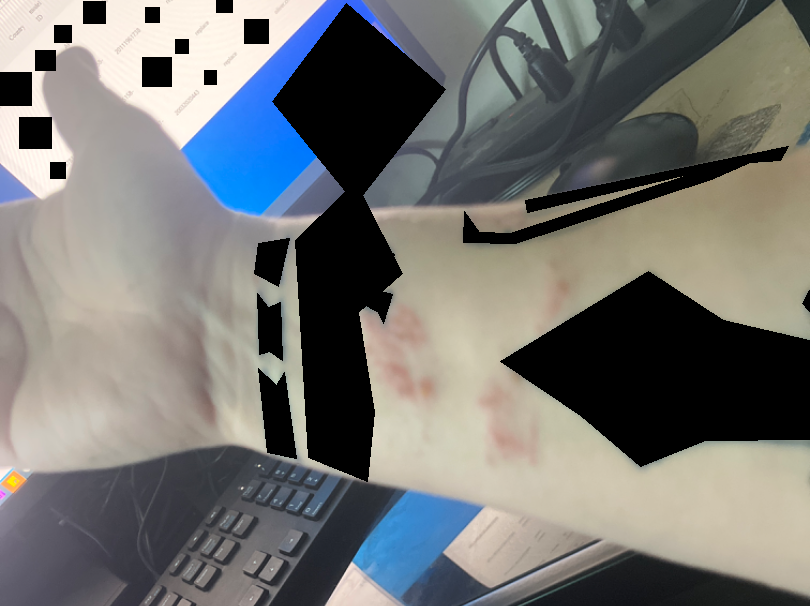Review: The skin findings could not be characterized from the image. Patient information: The patient considered this a rash. The arm is involved. An image taken at a distance. The condition has been present for less than one week. The lesion is associated with itching. The patient indicates the lesion is raised or bumpy and rough or flaky.